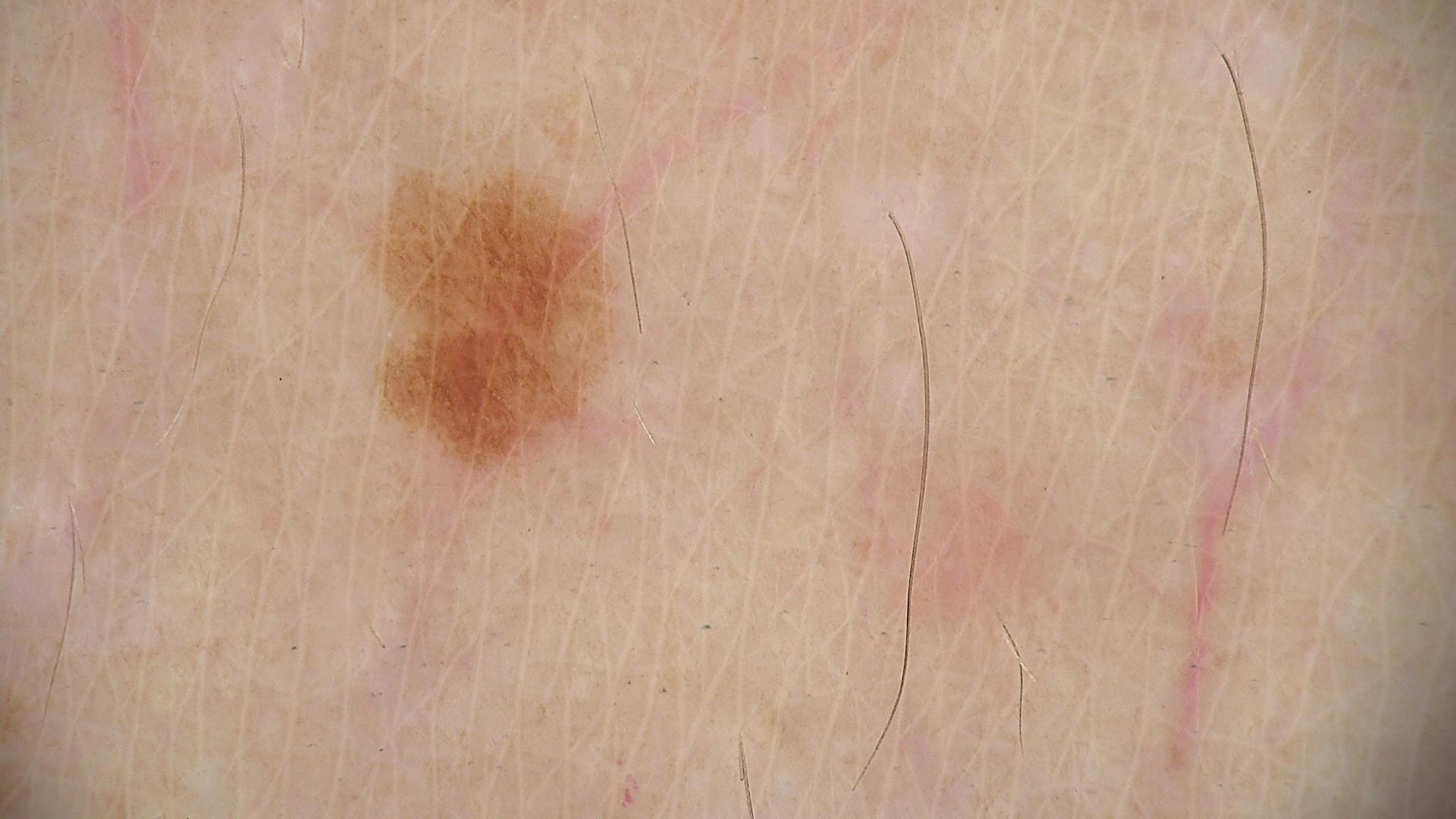Summary:
A dermoscopic image of a skin lesion.
Impression:
The diagnosis was a junctional nevus.